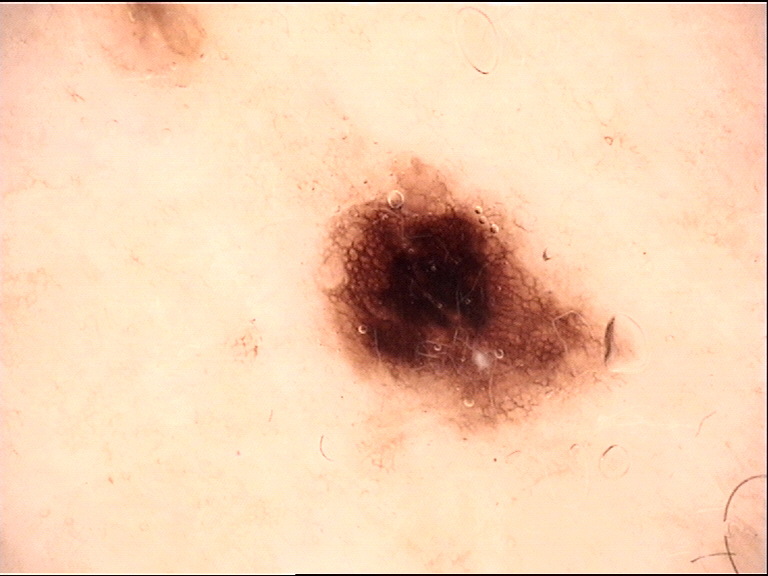Conclusion: Diagnosed as a dysplastic junctional nevus.